A skin lesion imaged with a dermatoscope: 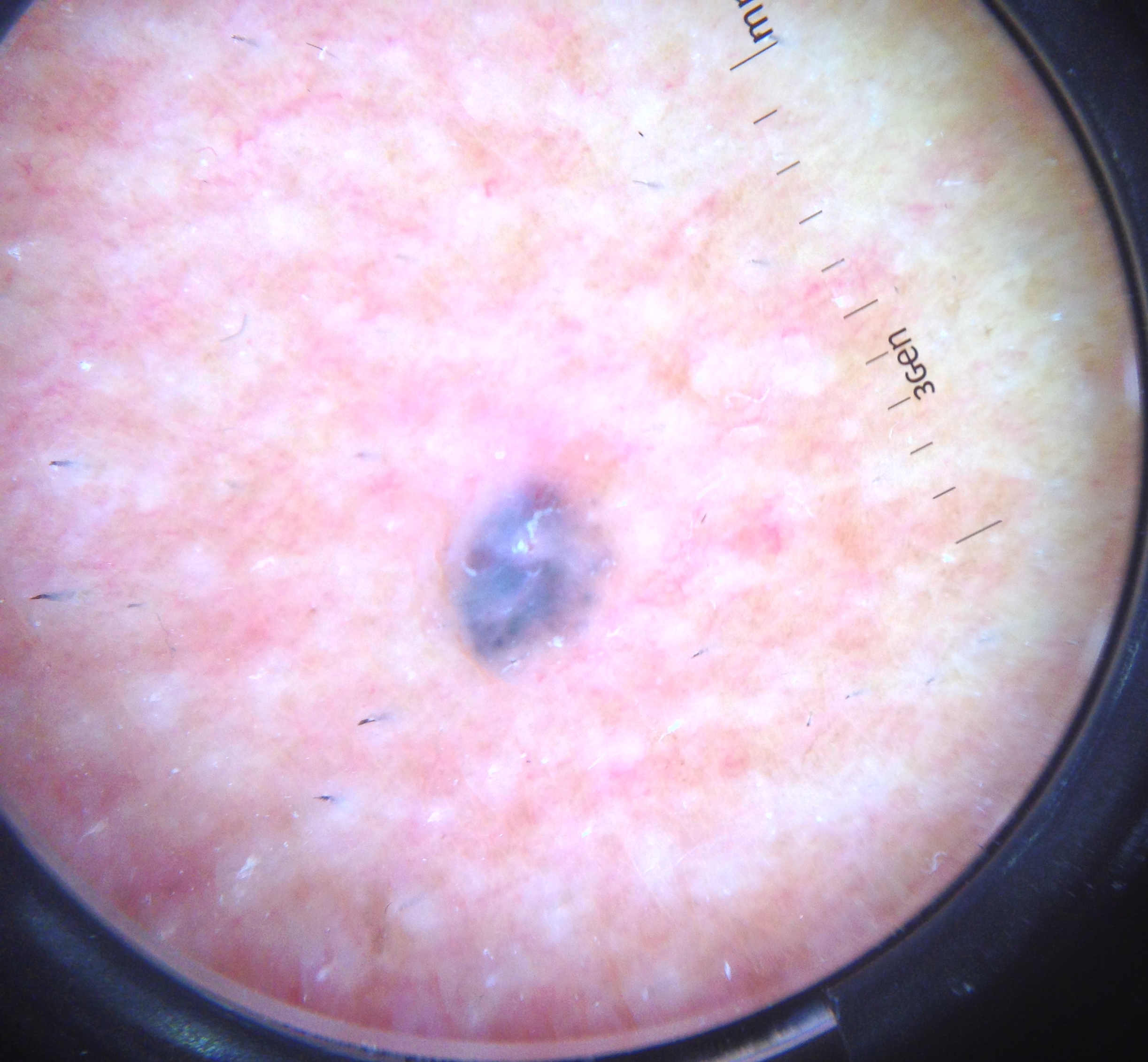This is a keratinocytic lesion. Histopathology confirmed a basal cell carcinoma.